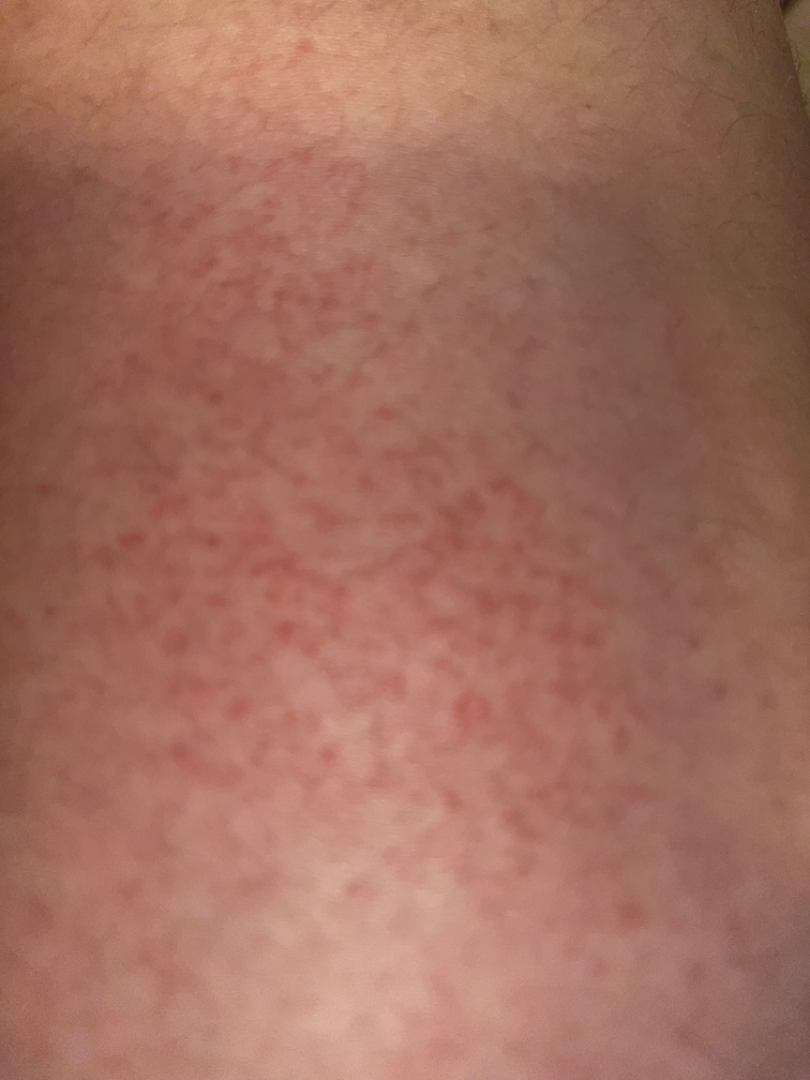Findings:
* self-categorized as · a rash
* anatomic site · leg
* lesion texture · flat
* duration · less than one week
* constitutional symptoms · none reported
* framing · close-up
* diagnostic considerations · favoring Irritant Contact Dermatitis; the differential also includes Eczema